A dermoscopic image of a skin lesion; a female patient 59 years old; referred for assessment of suspected melanocytic nevus; on a questionnaire the patient reported no personal history of cancer and no family history of skin cancer; the patient says their skin reddens with sun exposure; the patient describes having a moderate number of moles.
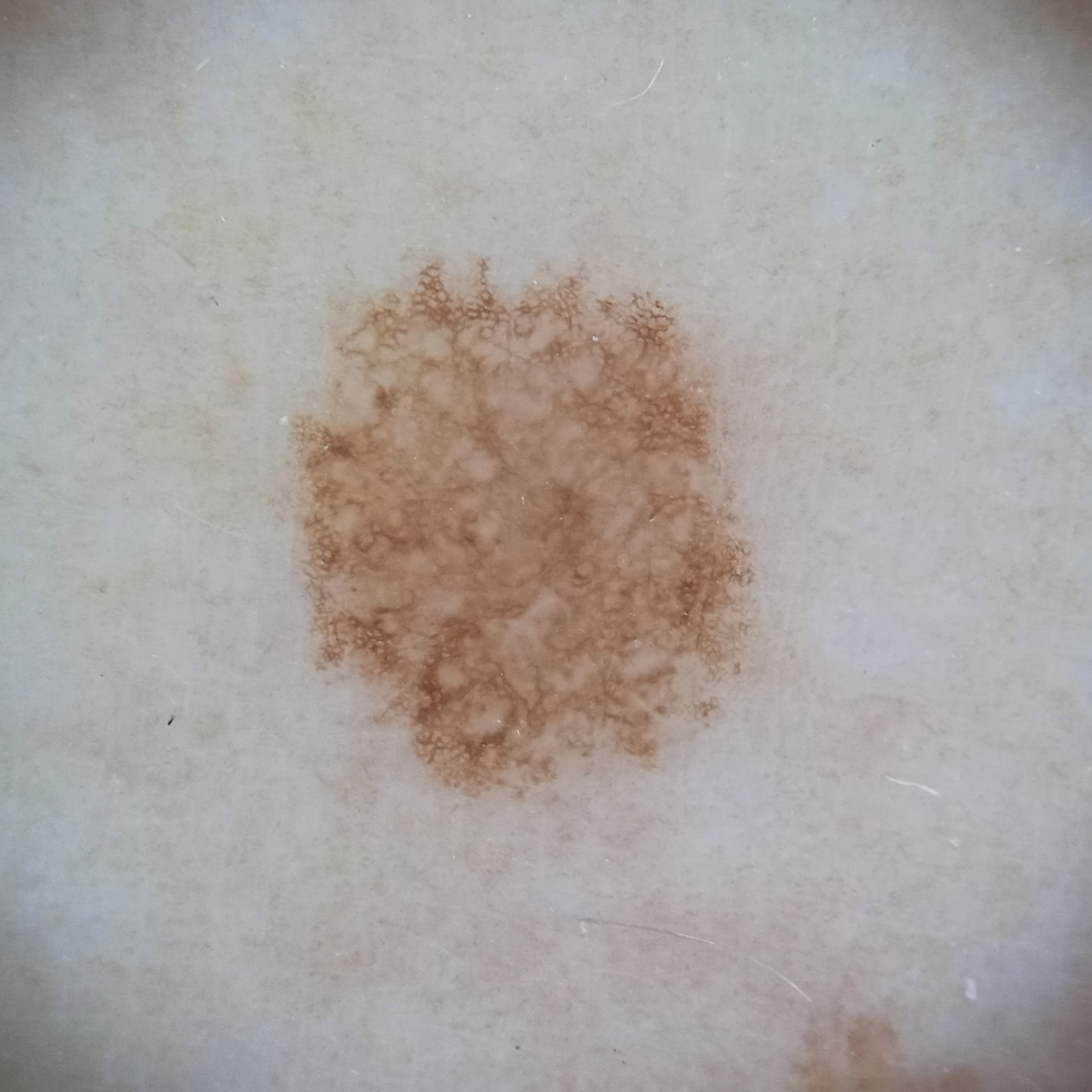Q: What is the anatomic site?
A: an arm
Q: What did the biopsy show?
A: atypical (dysplastic) nevus — biopsy-proven